Reported duration is one to four weeks. The patient reports the lesion is raised or bumpy. The patient described the issue as a rash. The affected area is the arm. This image was taken at an angle. Reported lesion symptoms include itching:
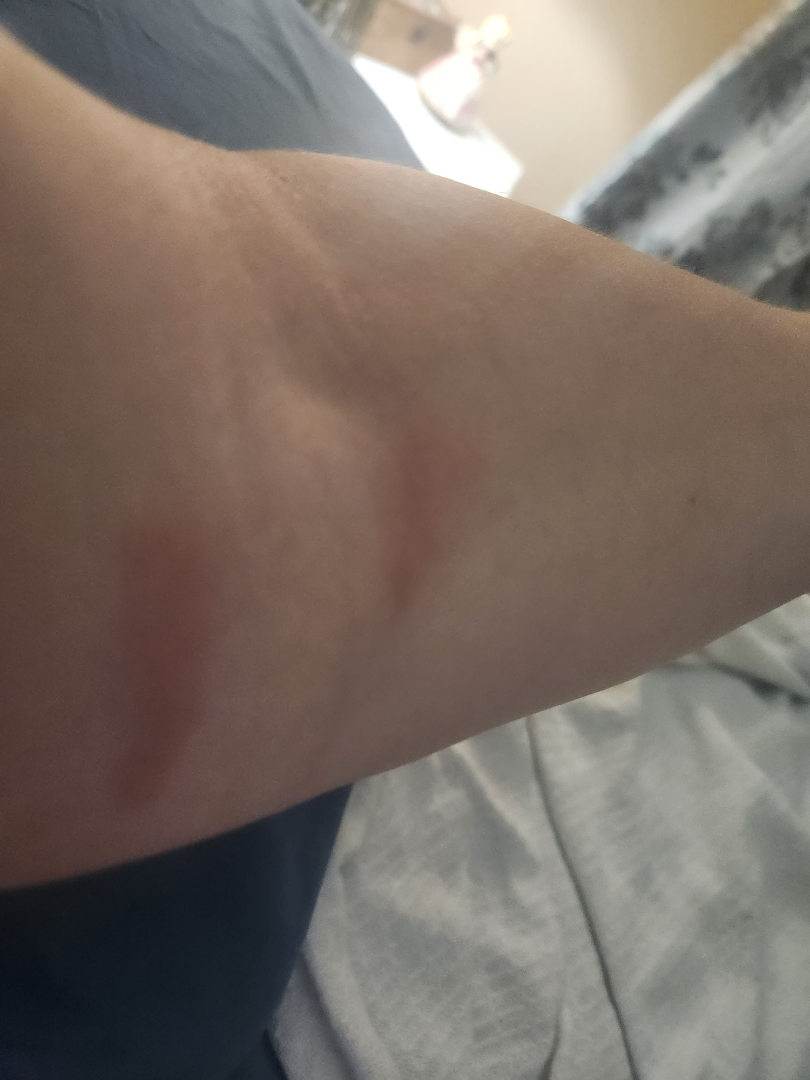Urticaria, Burn of skin and Allergic Contact Dermatitis were considered with similar weight.